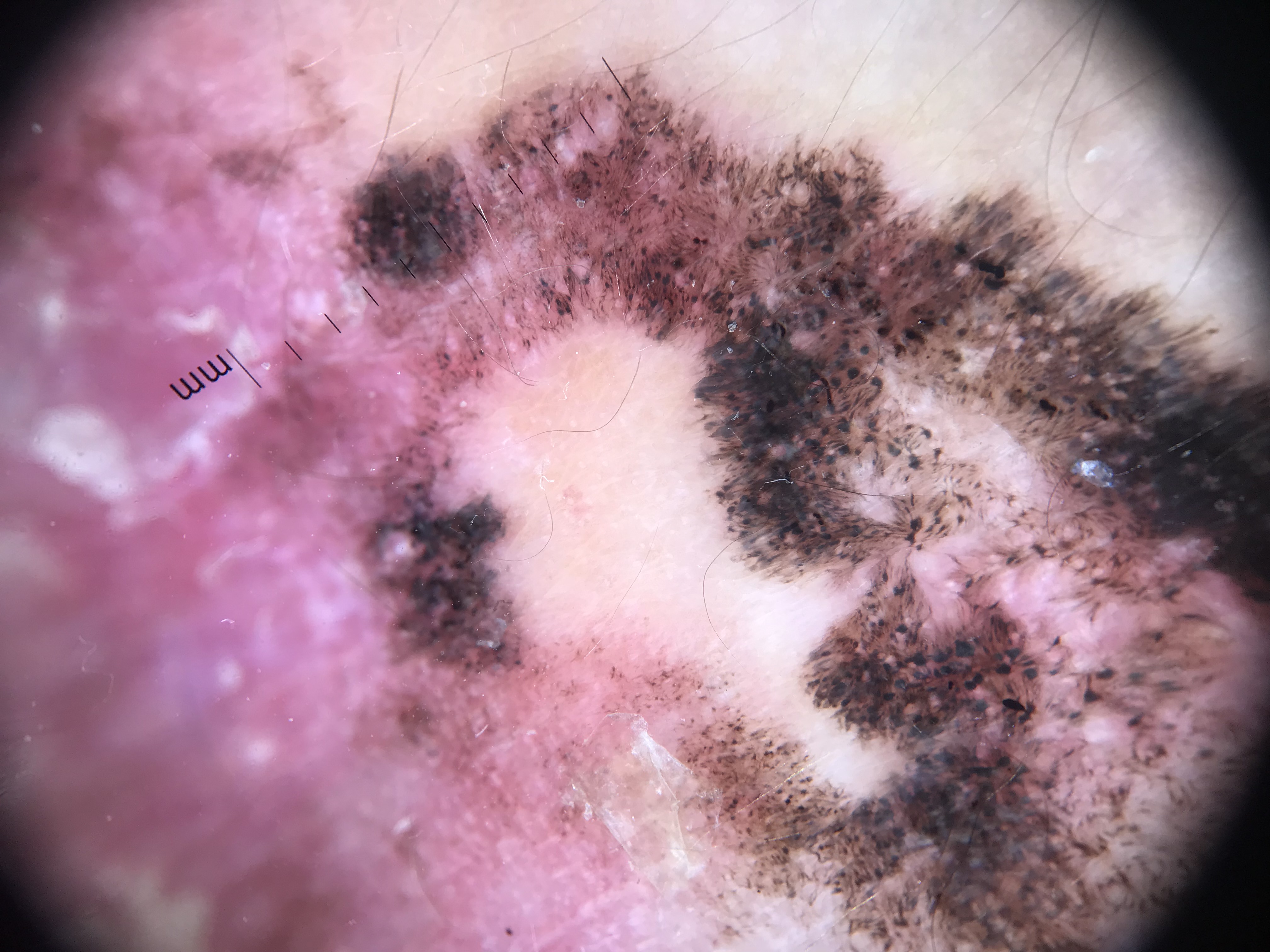Q: What is this lesion?
A: melanoma (biopsy-proven)